The lesion is described as raised or bumpy; self-categorized by the patient as a rash; located on the back of the torso; an image taken at an angle; female patient, age 18–29; the contributor notes burning — 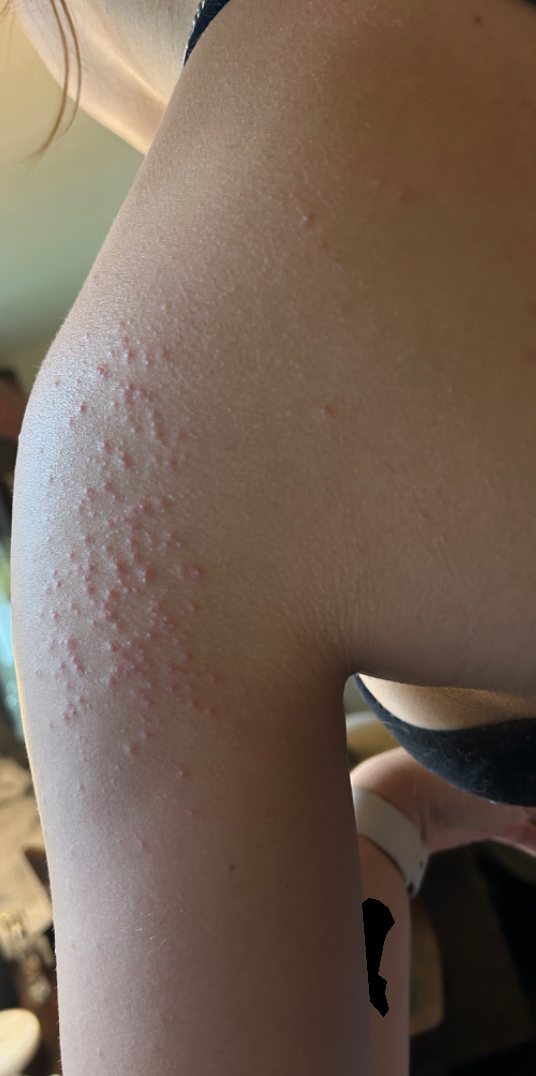assessment: not assessable